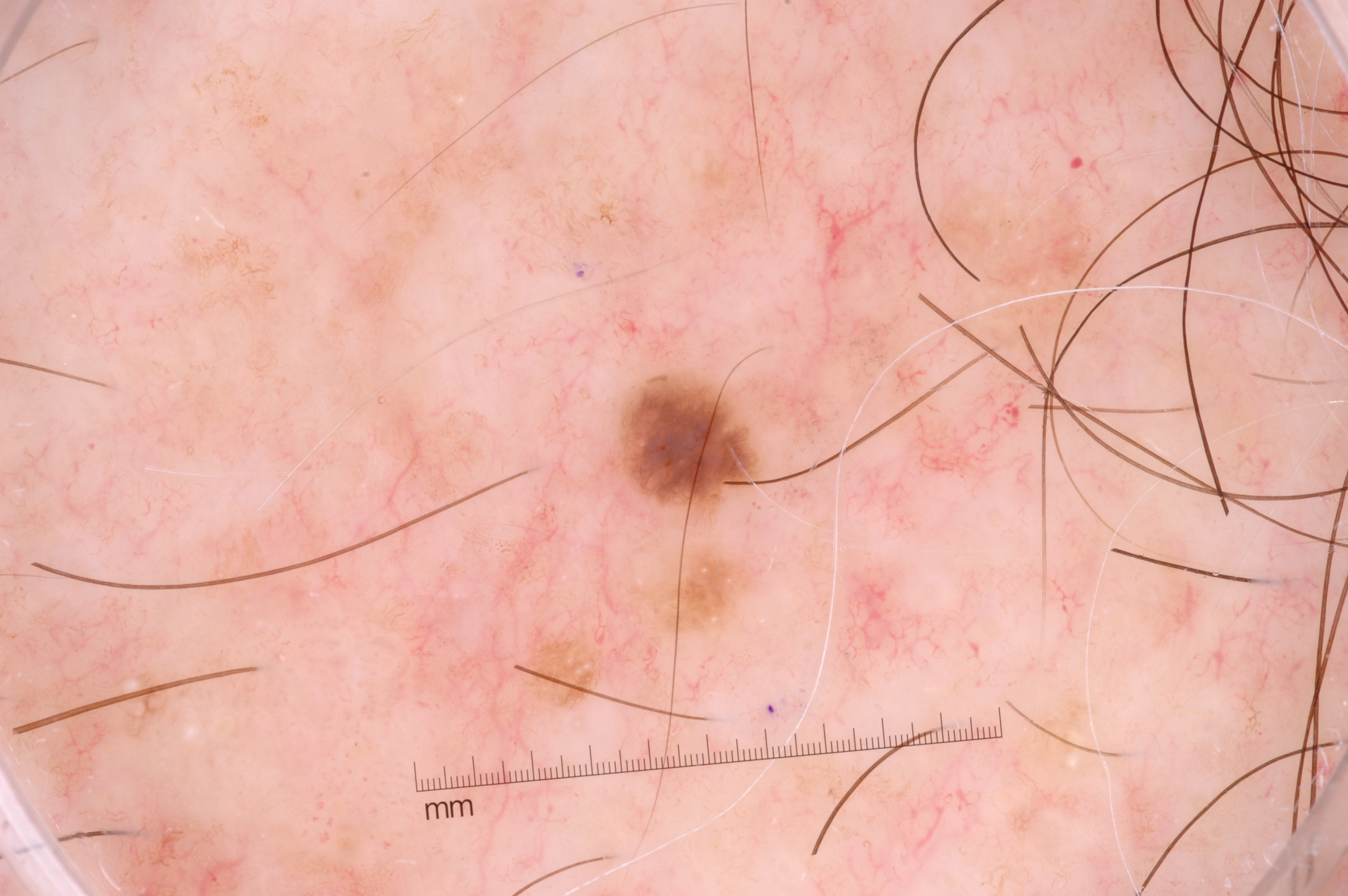A dermoscopy image of a single skin lesion. Lesion location: x1=611, y1=371, x2=758, y2=511. Dermoscopically, the lesion shows no streaks, negative network, pigment network, or milia-like cysts. Clinically diagnosed as a seborrheic keratosis.